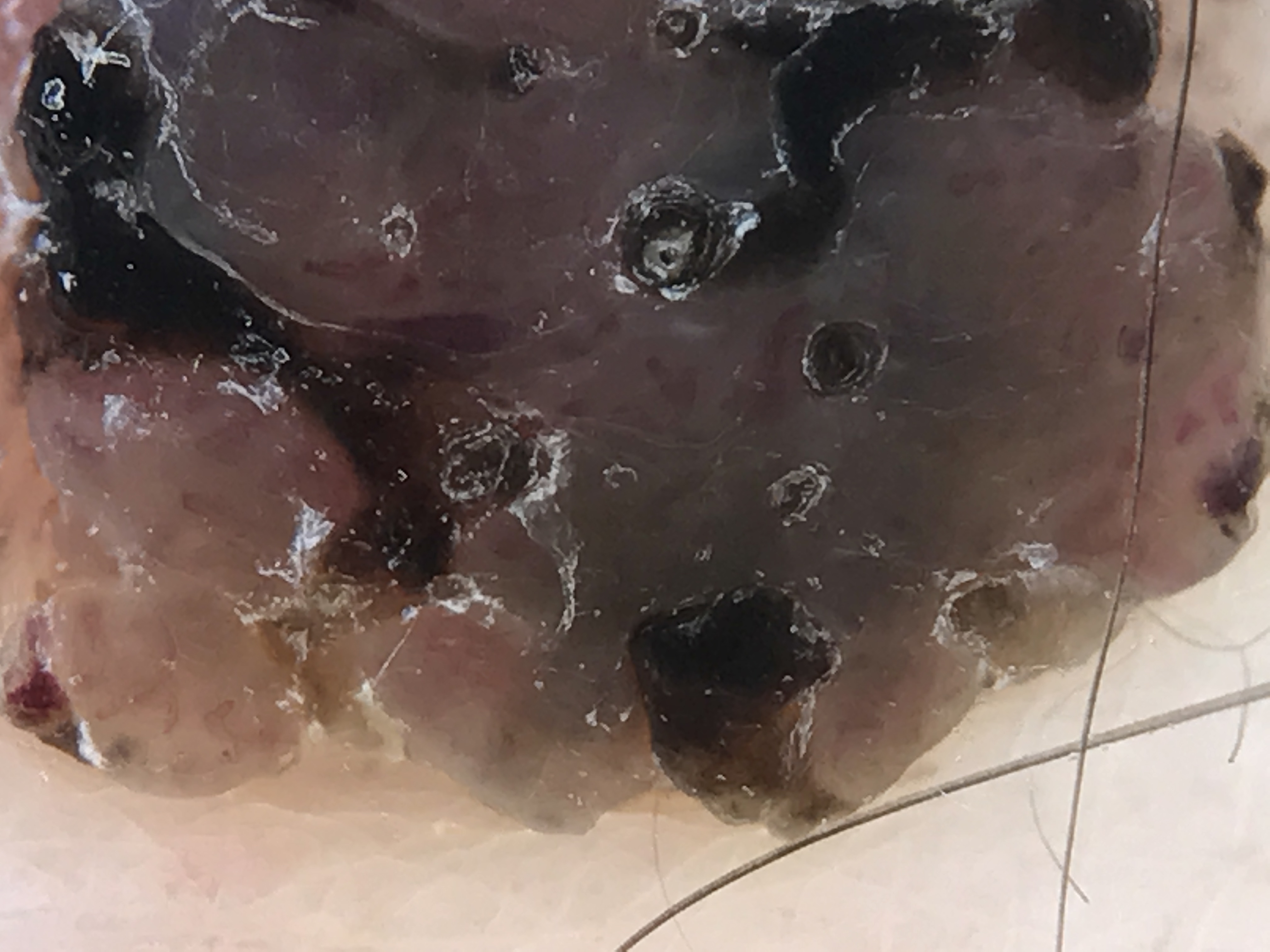diagnosis:
  name: congenital dysplastic compound nevus
  code: ccd
  malignancy: benign
  super_class: melanocytic
  confirmation: expert consensus